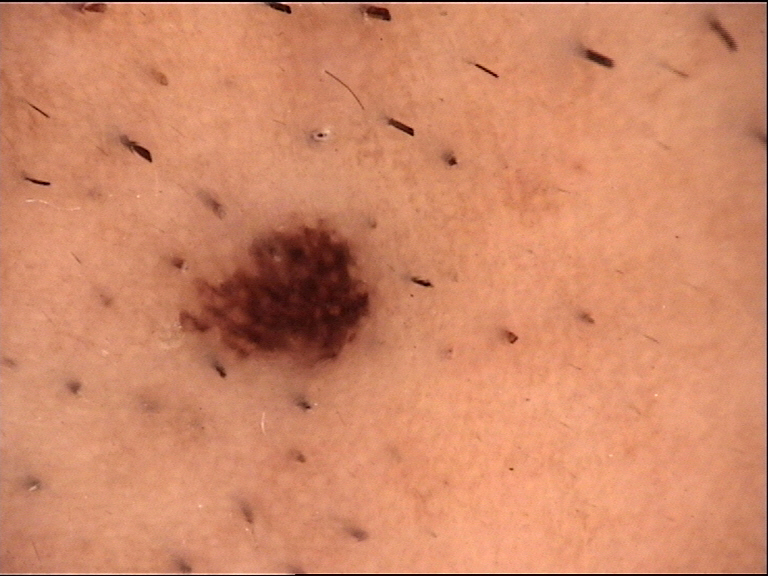label = Miescher nevus (expert consensus).